A dermoscopic close-up of a skin lesion:
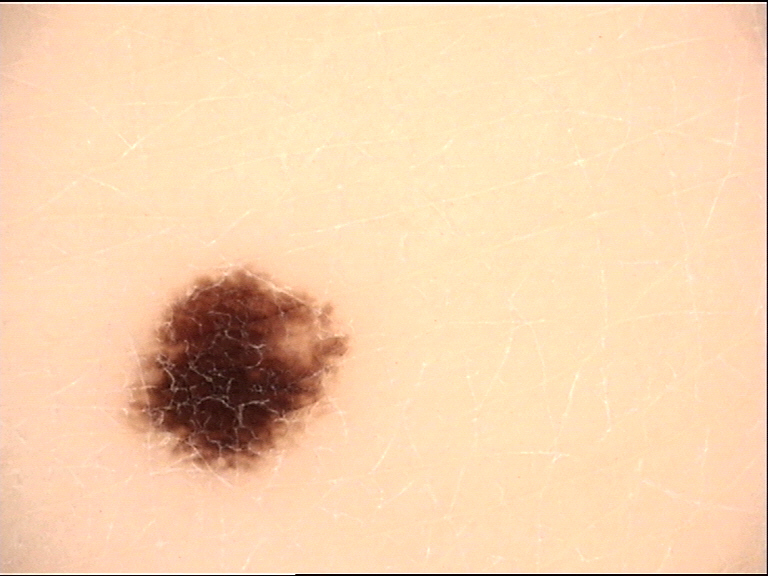Findings:
• diagnosis · acral dysplastic junctional nevus (expert consensus)